Located on the arm, front of the torso and leg · the subject is 18–29, male · this image was taken at an angle.
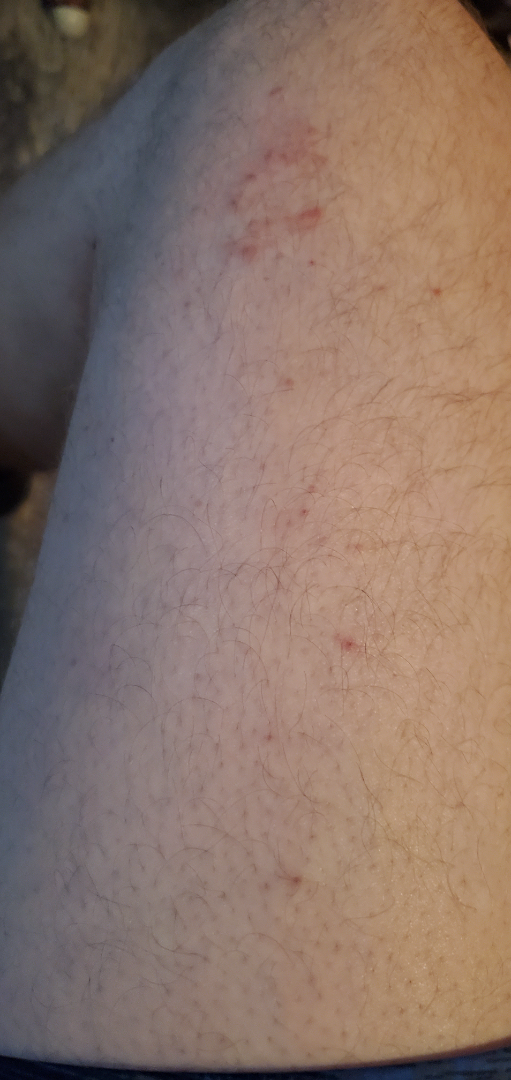The dermatologist could not determine a likely condition from the photograph alone.
Fitzpatrick III; human graders estimated Monk Skin Tone 2 or 3.
The lesion is described as raised or bumpy.
Symptoms reported: enlargement and itching.